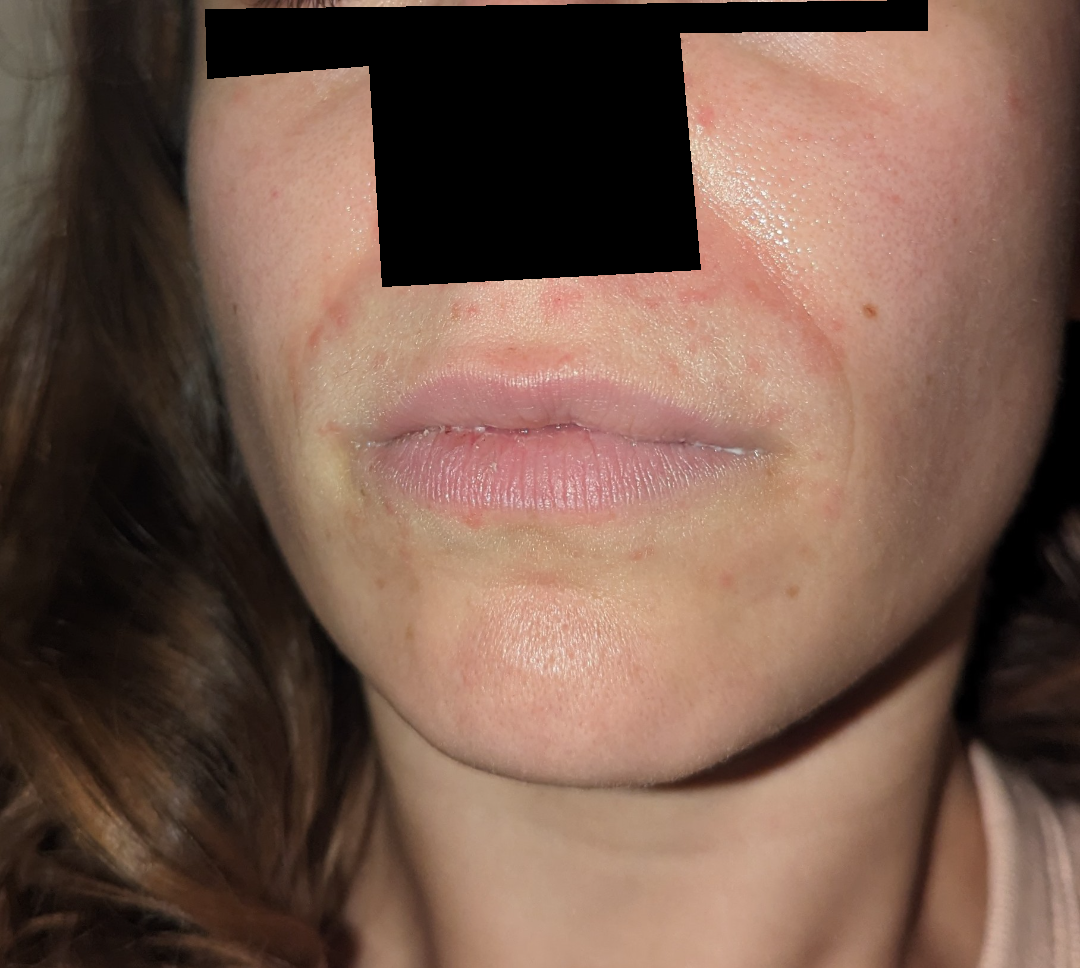The reviewer was unable to grade this case for skin condition. The patient is 30–39, female. The photo was captured at a distance. The affected area is the head or neck.